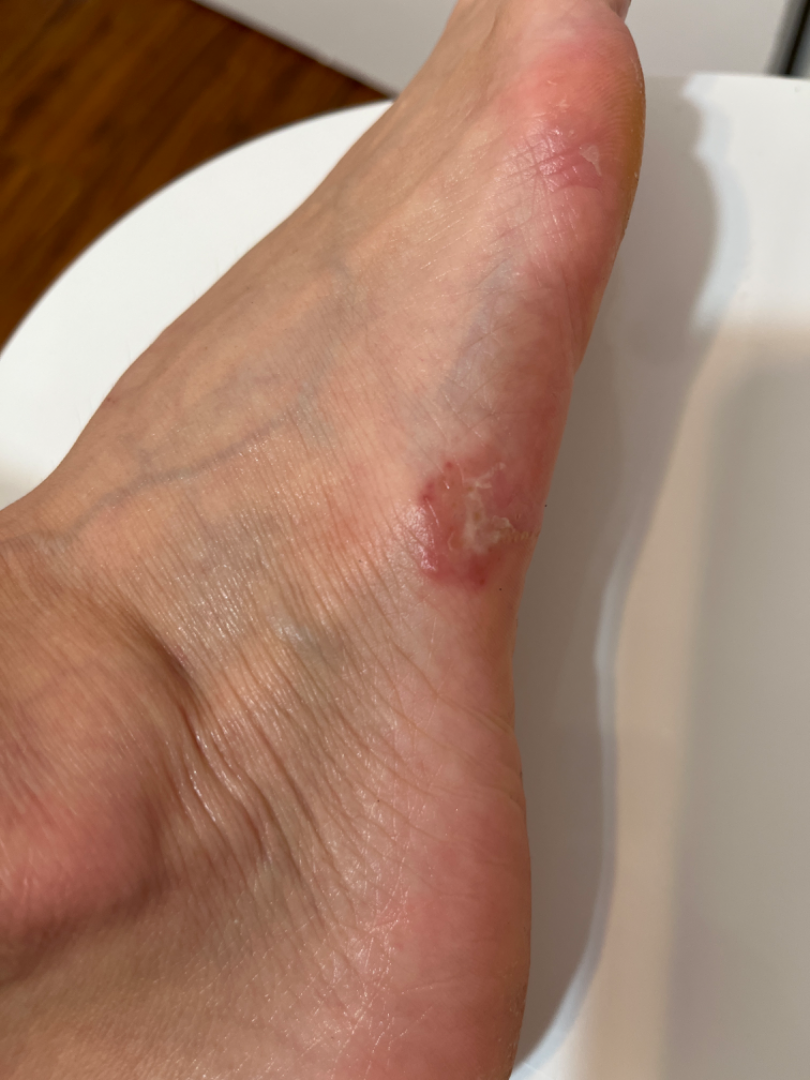The case was indeterminate on photographic review. Self-categorized by the patient as a rash. The condition has been present for one to four weeks. The top or side of the foot is involved. The contributor reports enlargement, bothersome appearance and itching. Female contributor, age 40–49. This is a close-up image. Self-reported Fitzpatrick skin type III.